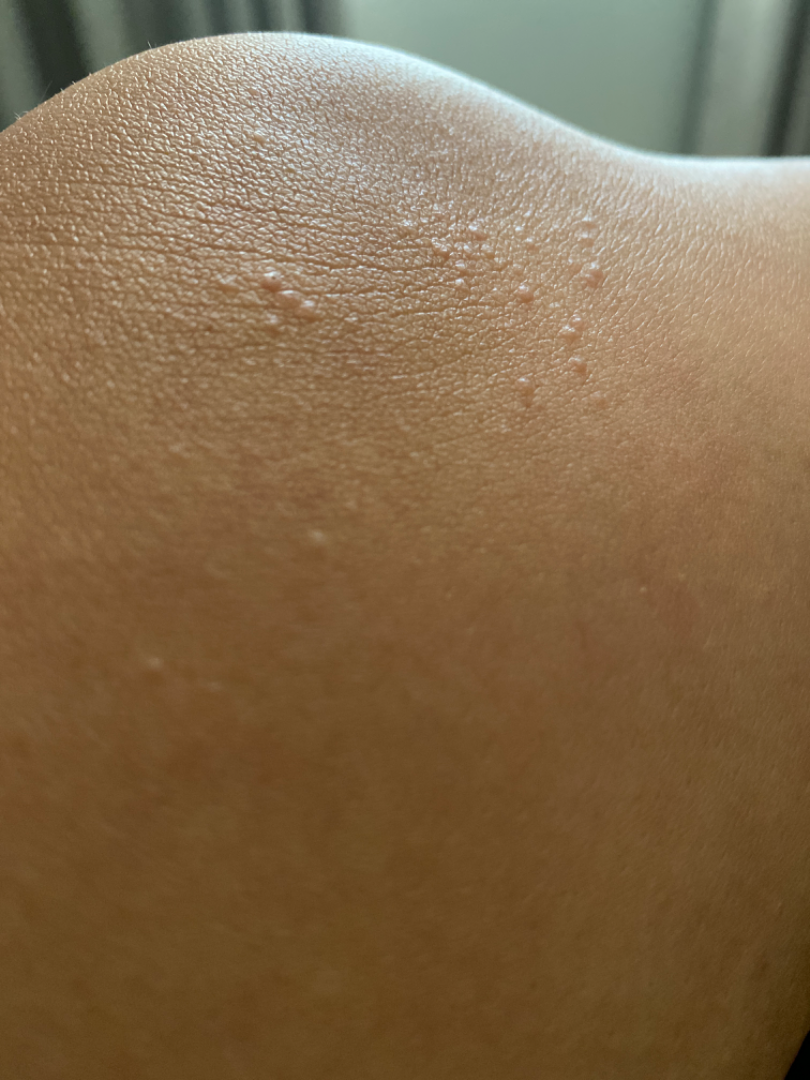The photograph was taken at an angle.
On teledermatology review: Lichen nitidus (most likely); Lichen planus/lichenoid eruption (considered); Molluscum Contagiosum (considered).